The patient is a male in their mid-50s; this is a dermoscopic photograph of a skin lesion.
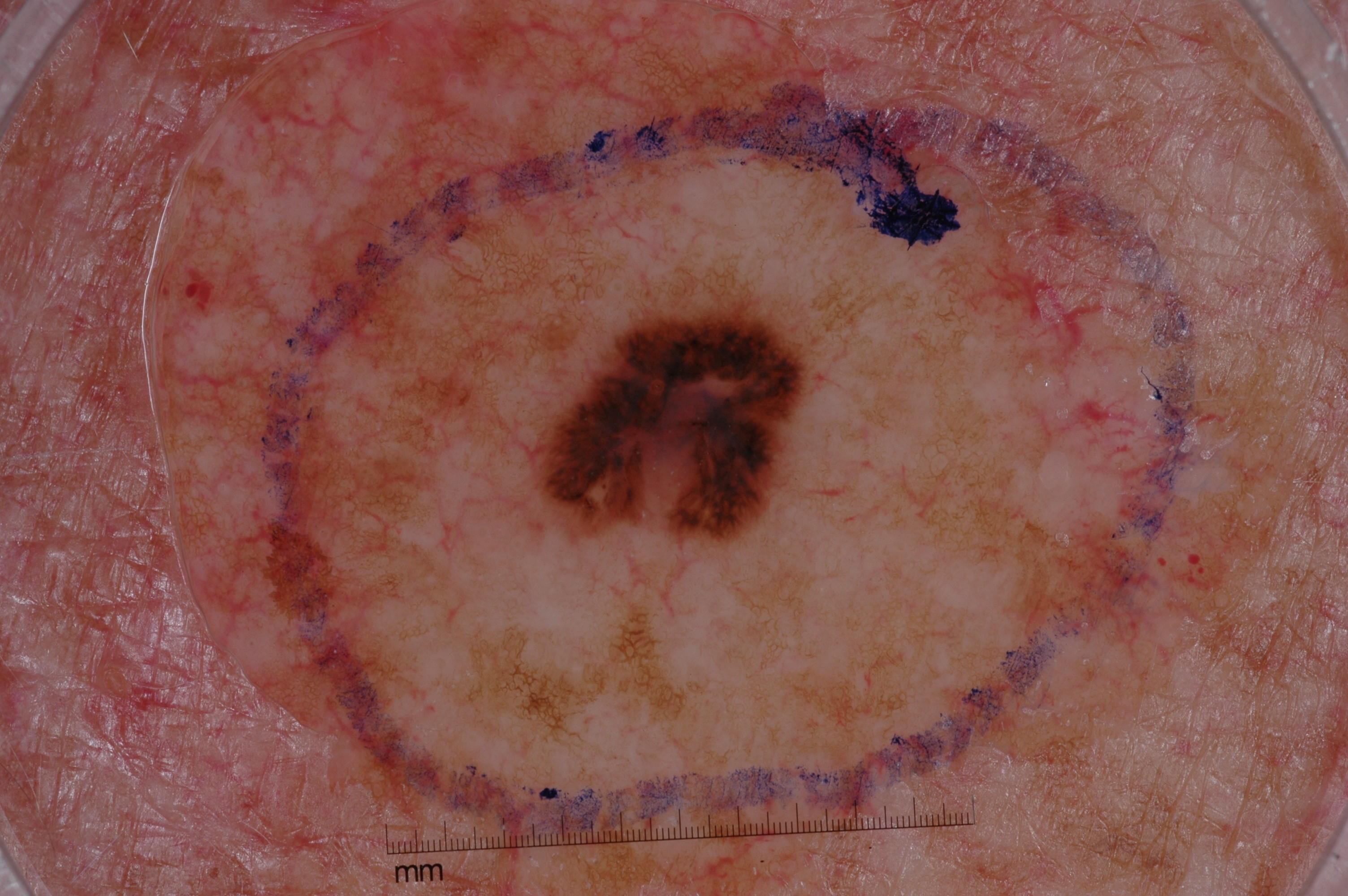  lesion_location:
    bbox_xyxy:
      - 531
      - 278
      - 809
      - 542
  dermoscopic_features:
    present: []
    absent:
      - milia-like cysts
      - streaks
      - pigment network
      - negative network
  lesion_extent: small
  diagnosis:
    name: melanoma
    malignancy: malignant
    lineage: melanocytic
    provenance: histopathology